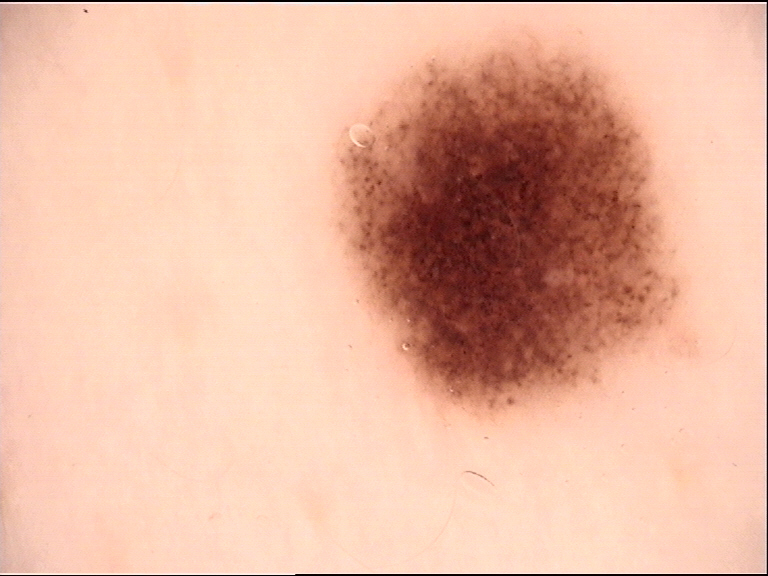A dermoscopic photograph of a skin lesion. Consistent with a benign lesion — a dysplastic junctional nevus.